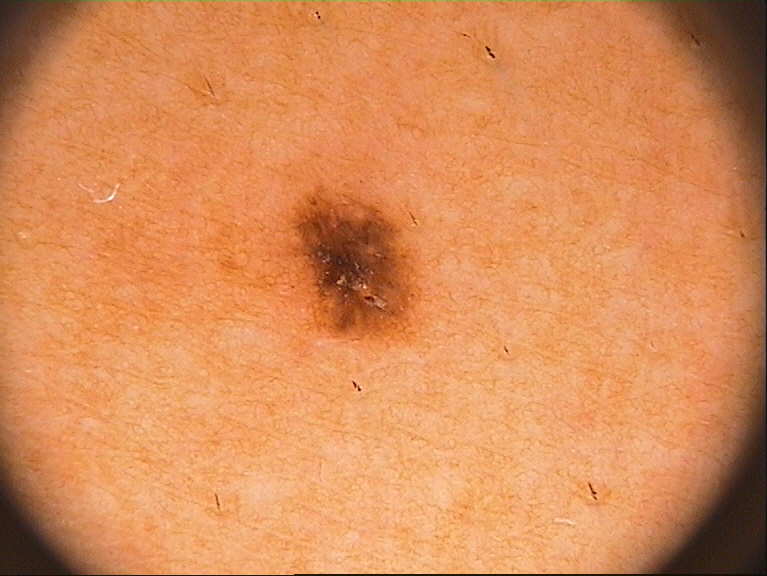Notes:
• patient — male, in their mid- to late 30s
• image — dermoscopy of a skin lesion
• dermoscopic features — pigment network
• location — bbox=[274, 184, 434, 351]
• impression — a melanocytic nevus, a benign skin lesion